The subject is female · the leg is involved · the photo was captured at an angle.
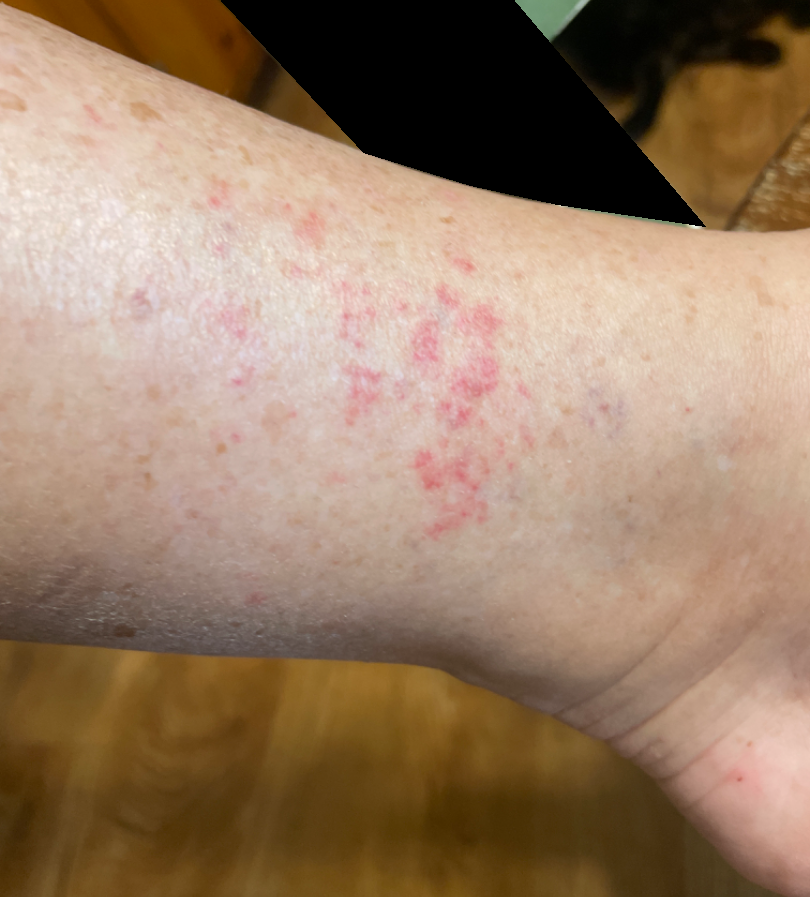other reported symptoms: none reported, lesion texture: flat, patient describes the issue as: skin that appeared healthy to them, patient-reported symptoms: none reported, duration: about one day, diagnostic considerations: Allergic Contact Dermatitis (possible); Stasis Dermatitis (possible); Eczema (possible); Contact dermatitis (possible).